A skin lesion imaged with a dermatoscope:
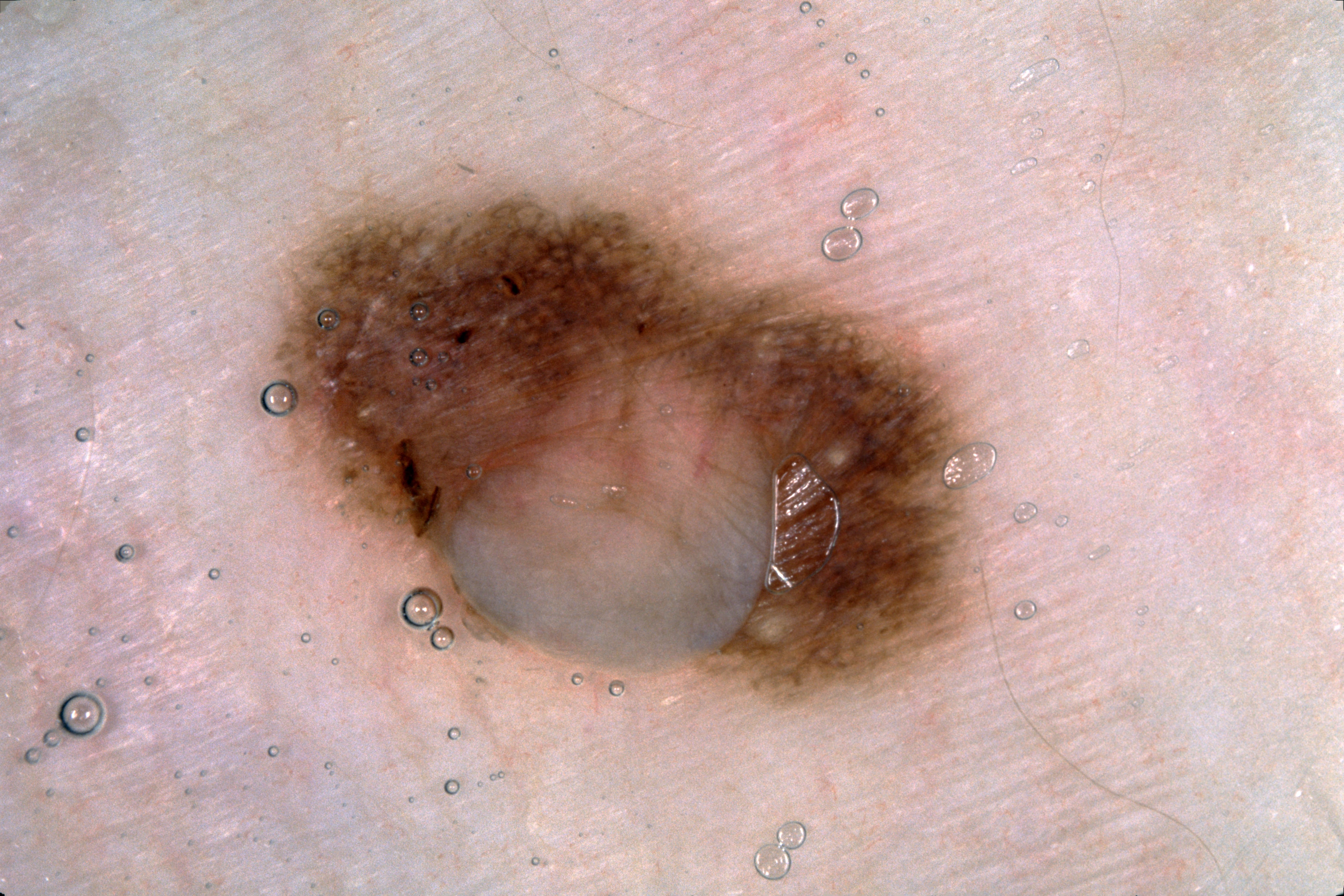{"lesion_location": {"bbox_xyxy": [259, 176, 988, 711]}, "dermoscopic_features": {"present": ["pigment network", "milia-like cysts"], "absent": ["negative network", "streaks"]}, "lesion_extent": "moderate", "diagnosis": {"name": "melanocytic nevus", "malignancy": "benign", "lineage": "melanocytic", "provenance": "clinical"}}